A dermoscopic close-up of a skin lesion.
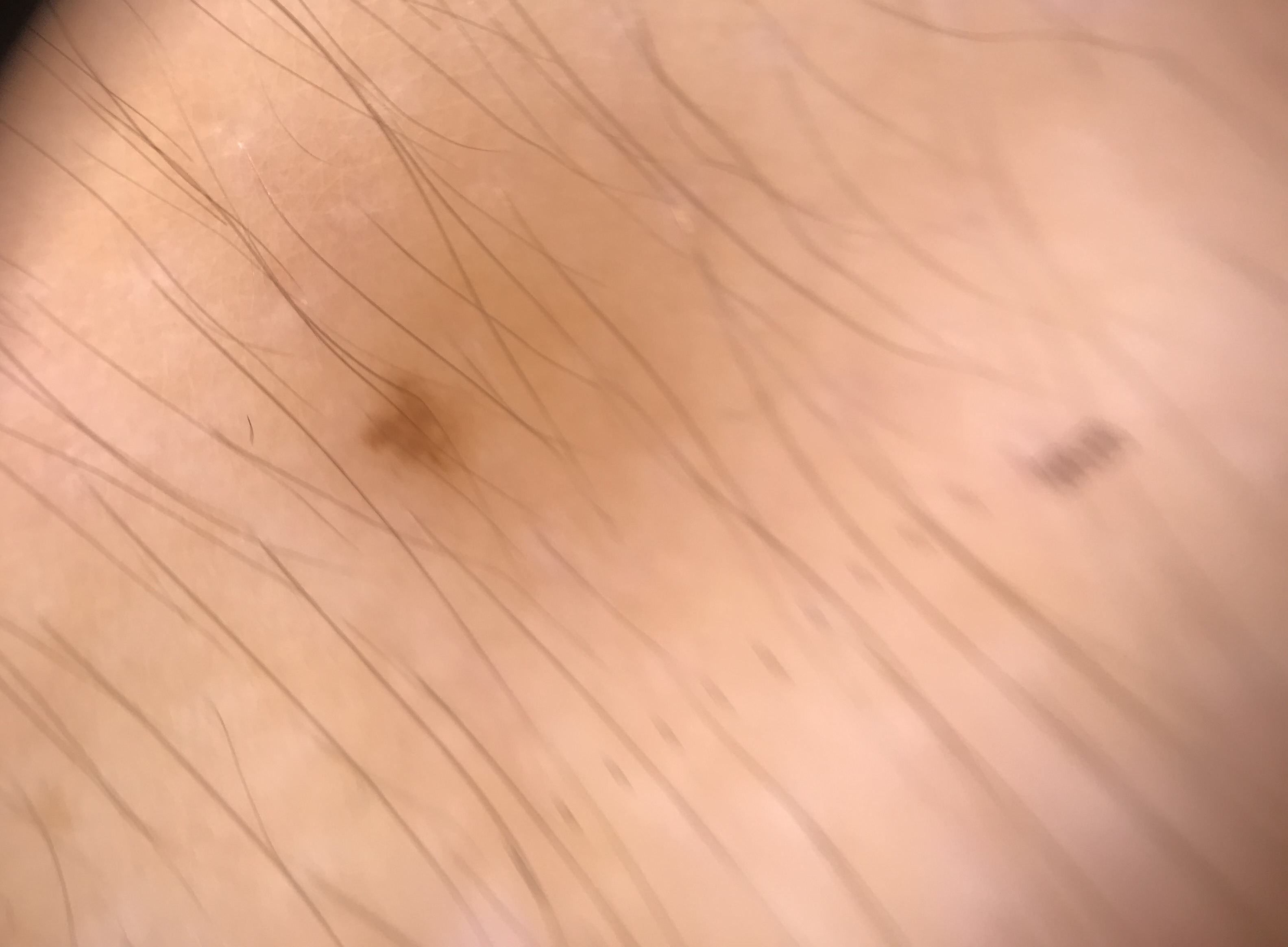The morphology is that of a banal lesion. The diagnosis was a junctional nevus.